The photograph is a close-up of the affected area · located on the arm and leg:
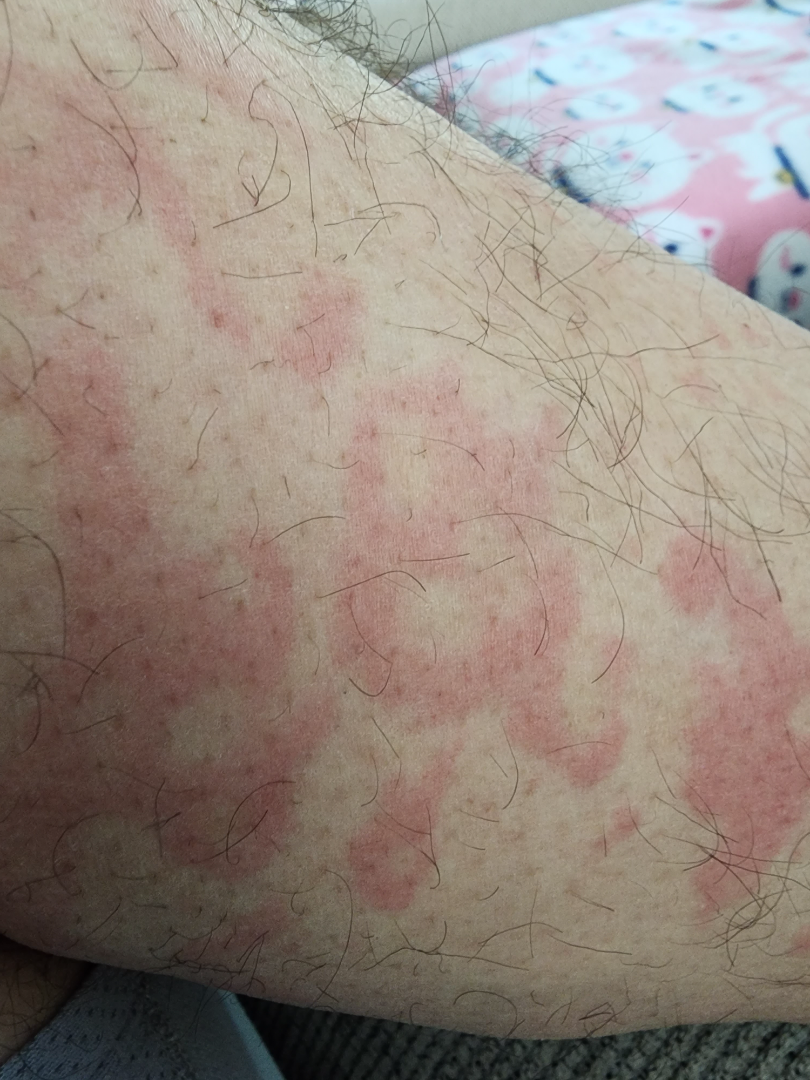Case summary:
- assessment · Urticaria (favored); Granuloma annulare (considered); Cutaneous lupus (considered)